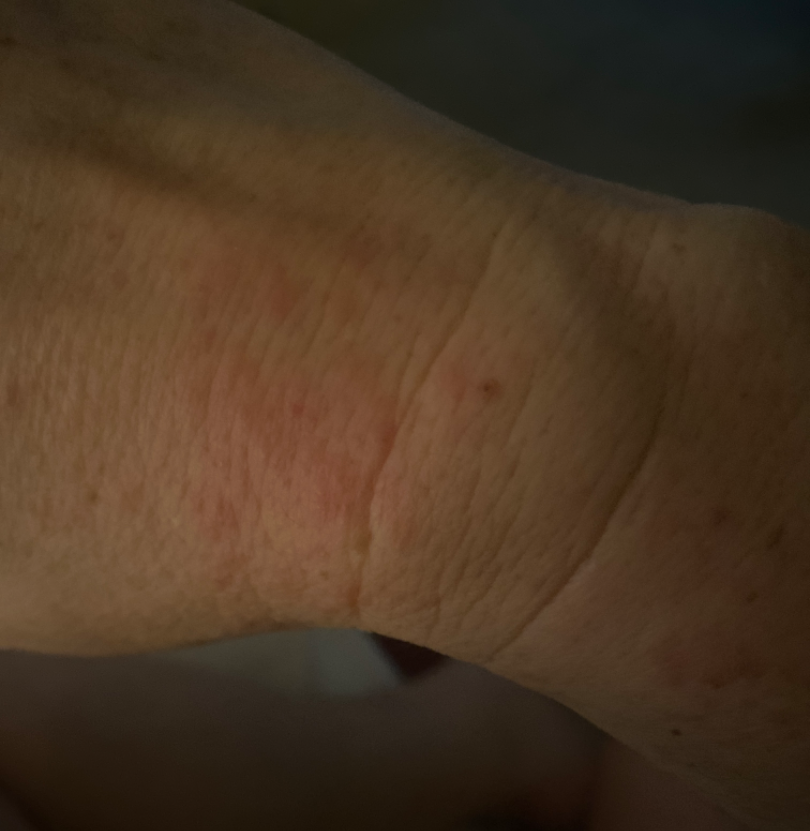Assessment:
The image was not sufficient for the reviewer to characterize the skin condition.
Clinical context:
The lesion is described as rough or flaky and raised or bumpy. The lesion is associated with itching. The patient considered this a rash. The contributor notes the condition has been present for less than one week. This is a close-up image.